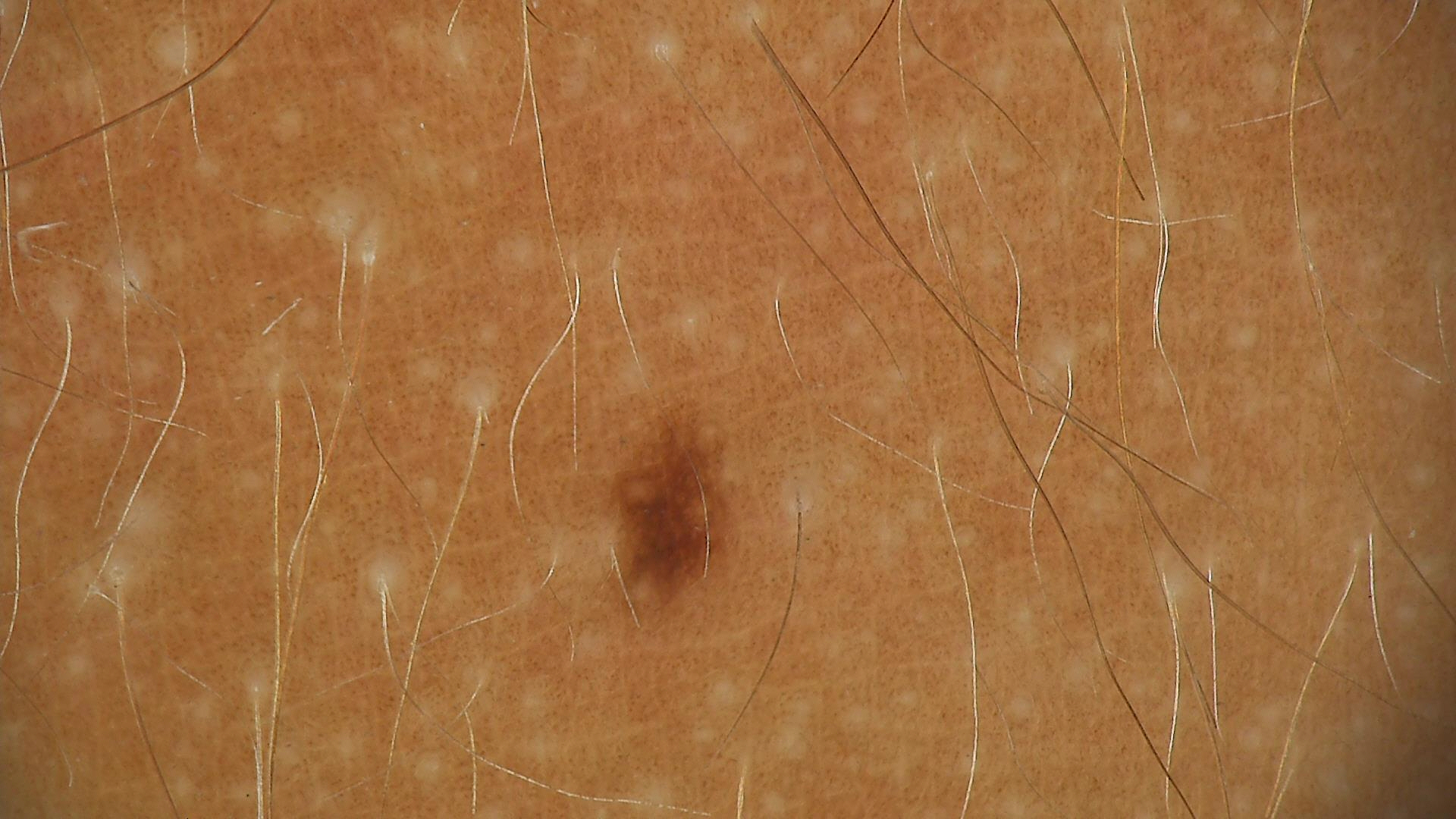<dermoscopy>
  <image>dermoscopy</image>
  <diagnosis>
    <name>dysplastic junctional nevus</name>
    <code>jd</code>
    <malignancy>benign</malignancy>
    <super_class>melanocytic</super_class>
    <confirmation>expert consensus</confirmation>
  </diagnosis>
</dermoscopy>